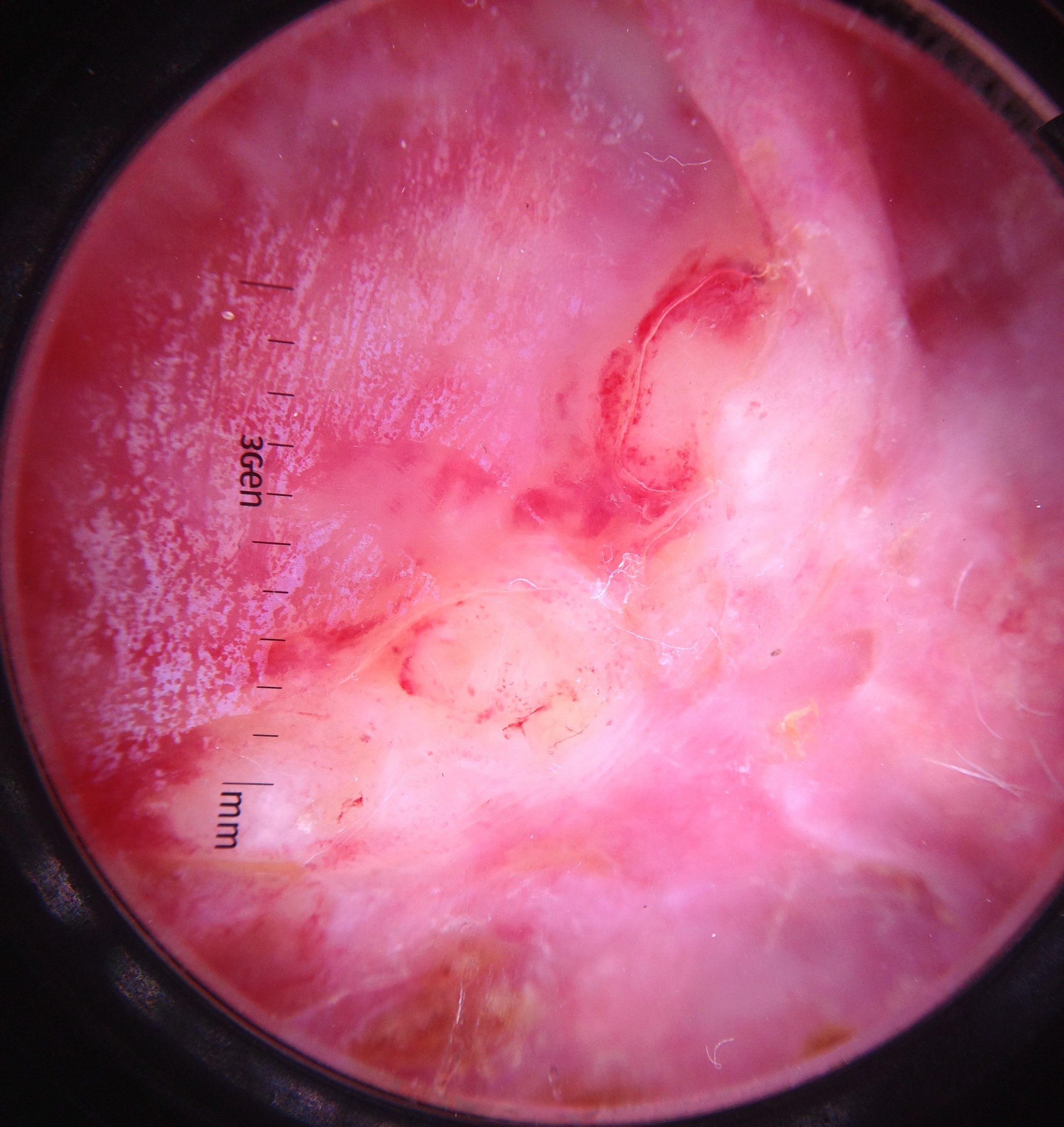A skin lesion imaged with a dermatoscope. Biopsy-confirmed as a squamous cell carcinoma.